An image taken at a distance. The affected area is the arm and top or side of the foot.
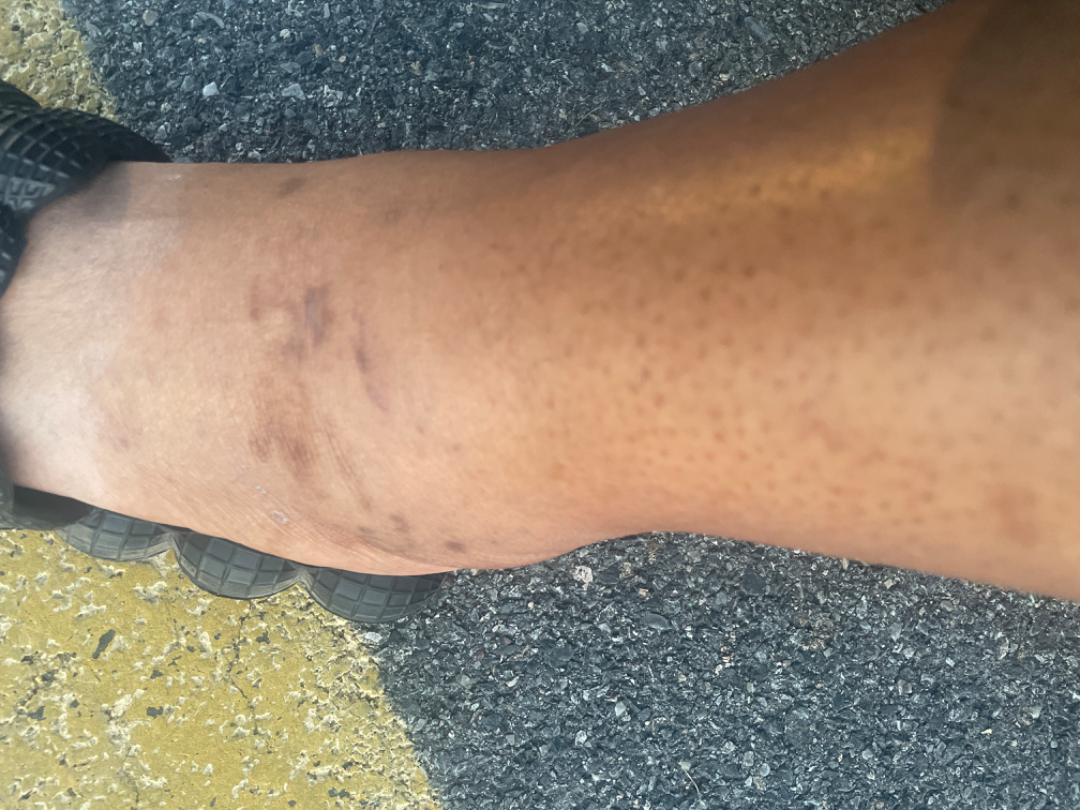The patient described the issue as a rash.
Reported duration is three to twelve months.
The patient notes the lesion is rough or flaky.
The lesion is associated with itching, bothersome appearance and darkening.
Single-reviewer assessment: most likely Lichen planus/lichenoid eruption; an alternative is Chronic dermatitis, NOS; with consideration of Drug Rash.